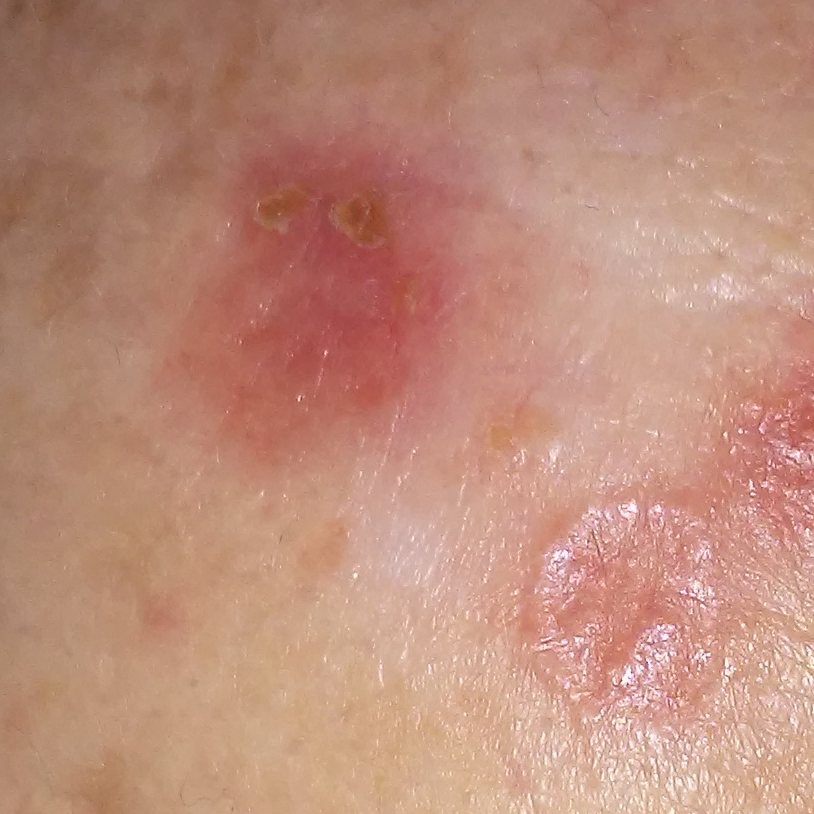{
  "patient": {
    "age": 51,
    "gender": "female"
  },
  "image": "clinical photograph",
  "skin_type": "I",
  "risk_factors": {
    "positive": [
      "prior skin cancer (patient or family)"
    ]
  },
  "lesion_location": "the chest",
  "symptoms": {
    "present": [
      "growth",
      "itching",
      "bleeding"
    ],
    "absent": [
      "pain"
    ]
  },
  "diagnosis": {
    "name": "basal cell carcinoma",
    "code": "BCC",
    "malignancy": "malignant",
    "confirmation": "histopathology"
  }
}